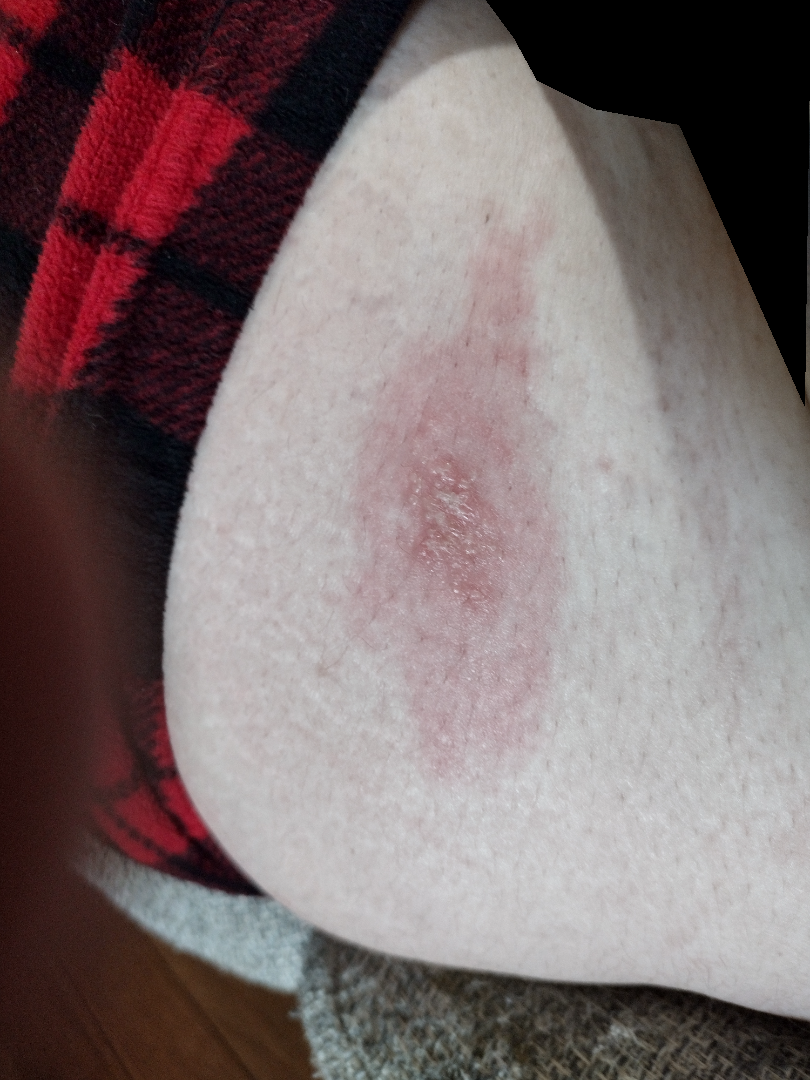History: The lesion is described as raised or bumpy. The leg is involved. The photograph is a close-up of the affected area. The patient reports pain, enlargement and burning. The patient also reports fatigue. Present for less than one week. Impression: On photographic review: Acute dermatitis, NOS and Drug Rash were considered with similar weight.